A female subject aged around 60. The patient was assessed as Fitzpatrick II. A dermoscopic photograph of a skin lesion.
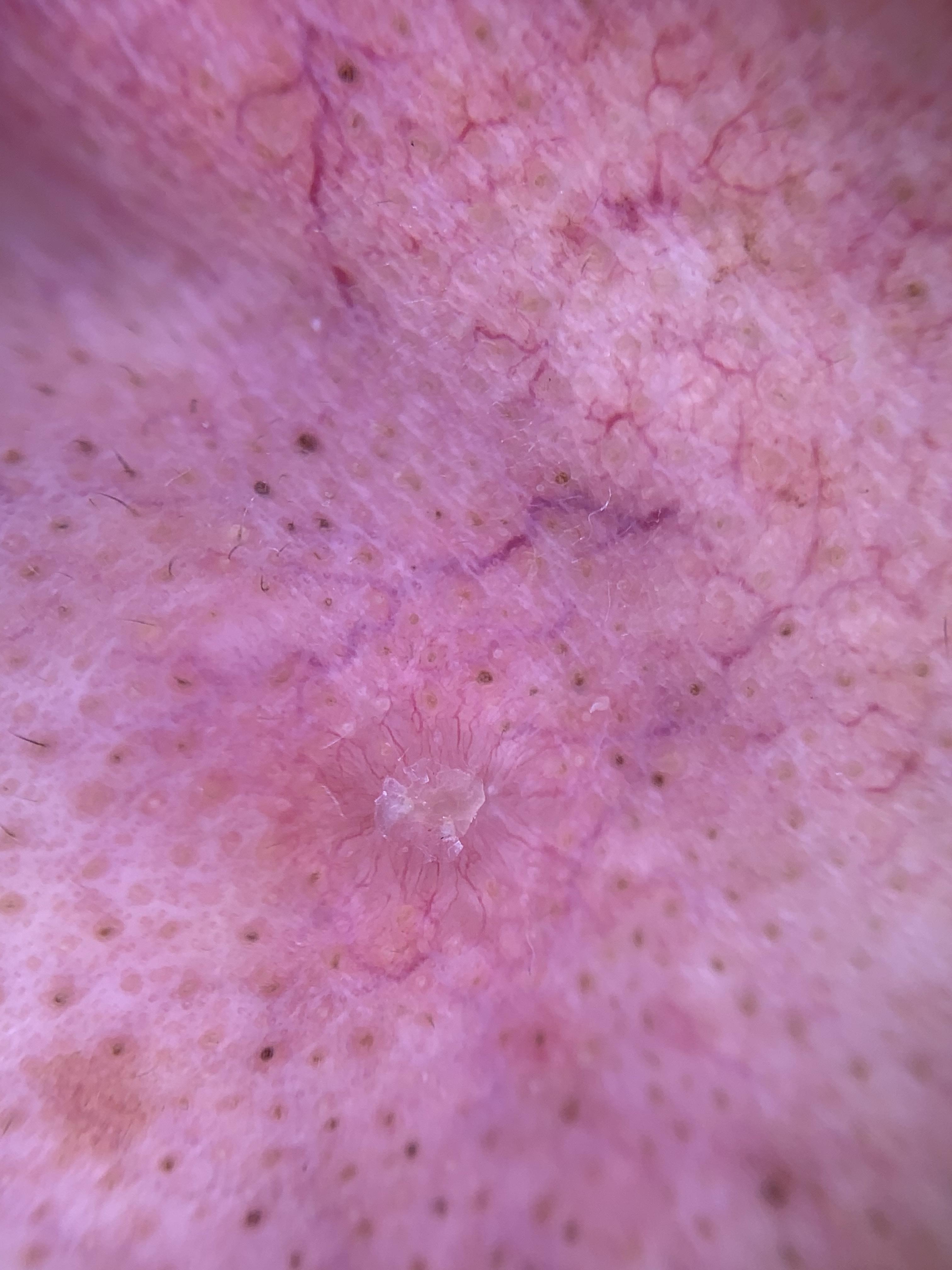Summary: The lesion was found on the head or neck. Conclusion: Histopathological examination showed a malignant, adnexal lesion — a basal cell carcinoma.